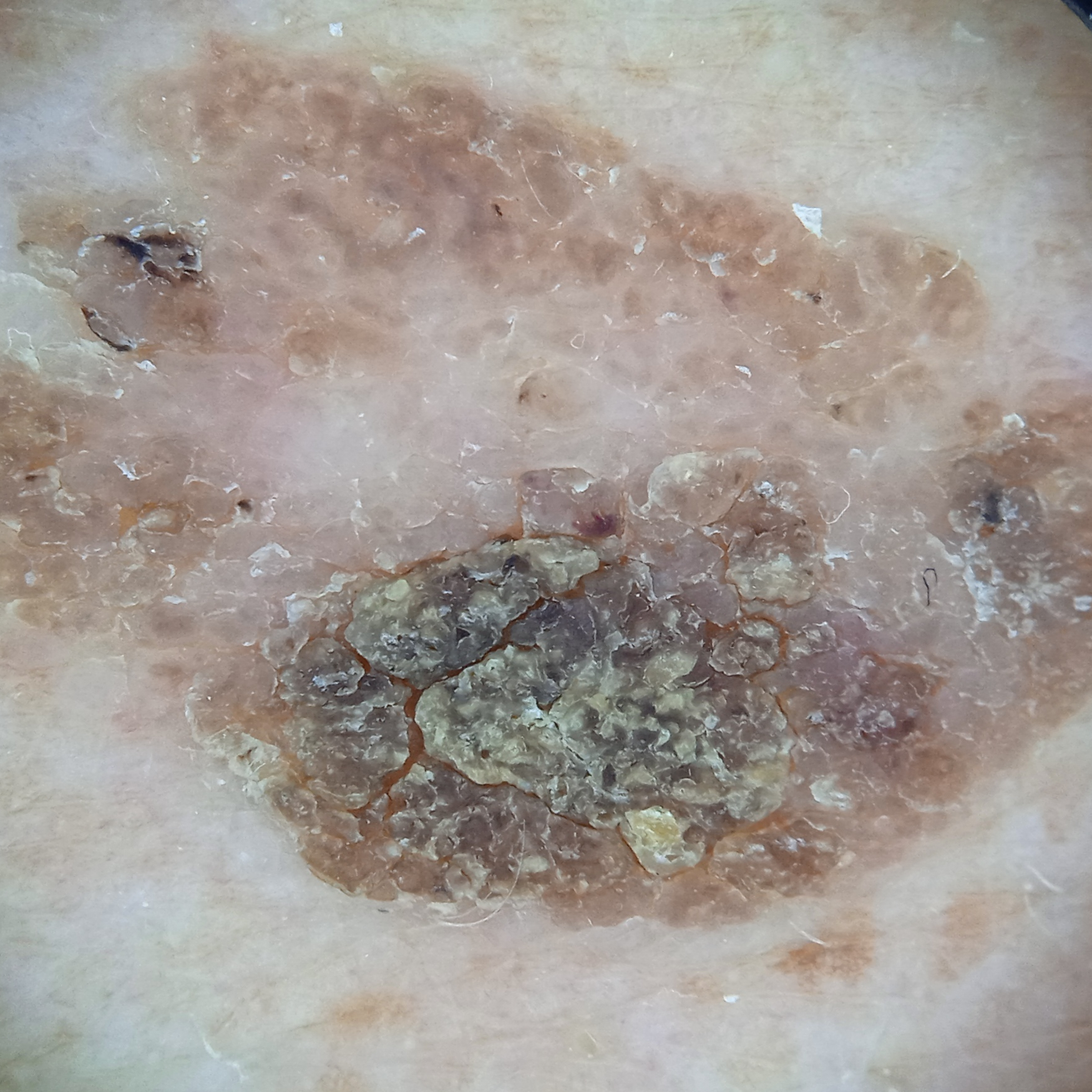The four-dermatologist consensus diagnosis was a seborrheic keratosis.